A skin lesion imaged with a dermatoscope.
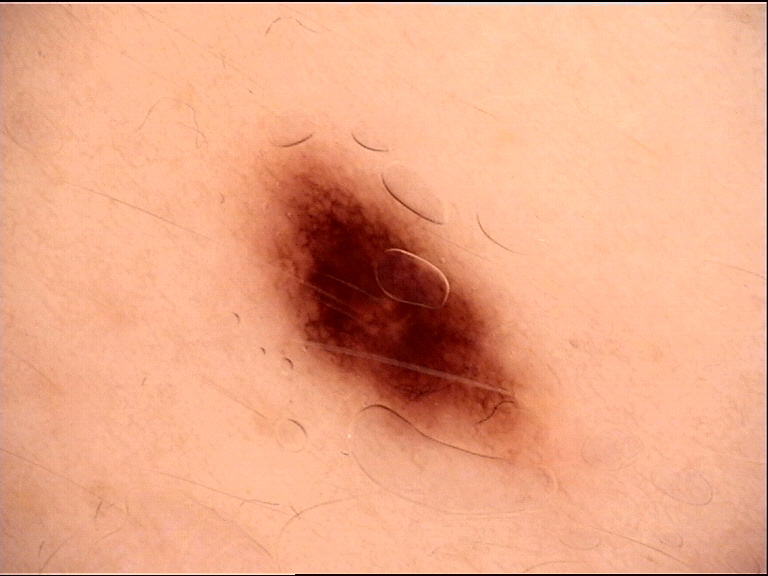- label · dysplastic junctional nevus (expert consensus)